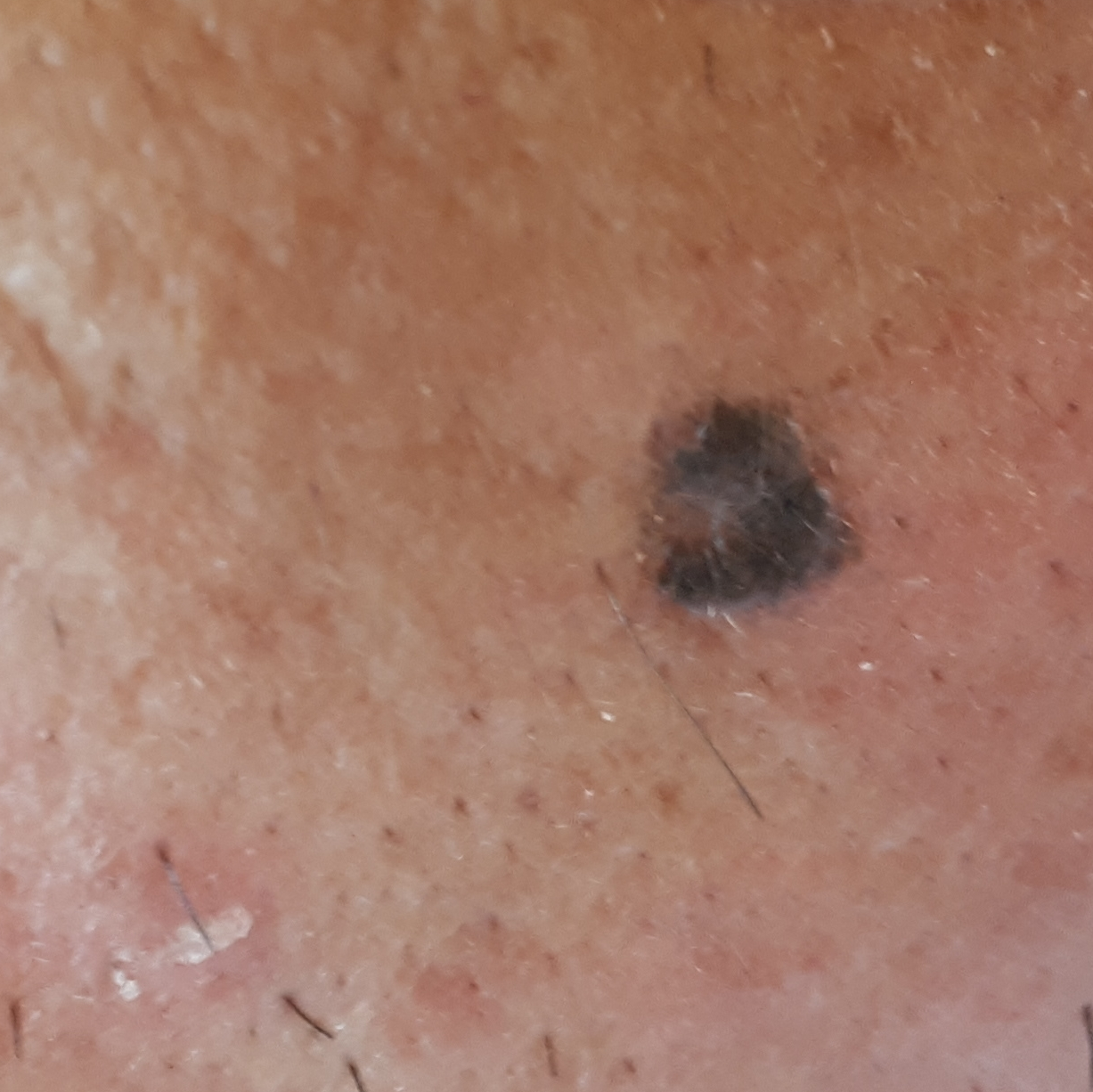A subject in their early 50s.
The lesion was found on the face.
Per patient report, the lesion has grown and is elevated.
Consistent with a benign skin lesion — a seborrheic keratosis.